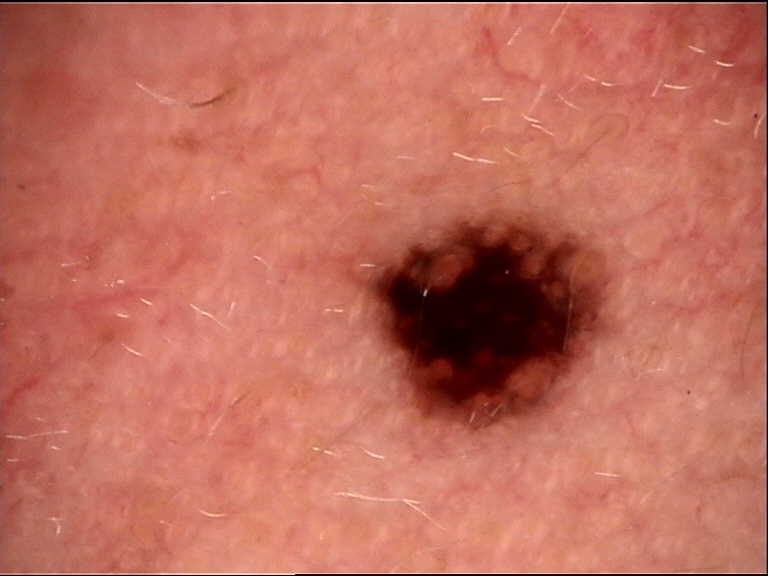Dermoscopy of a skin lesion.
The diagnosis was a banal lesion — a compound nevus.